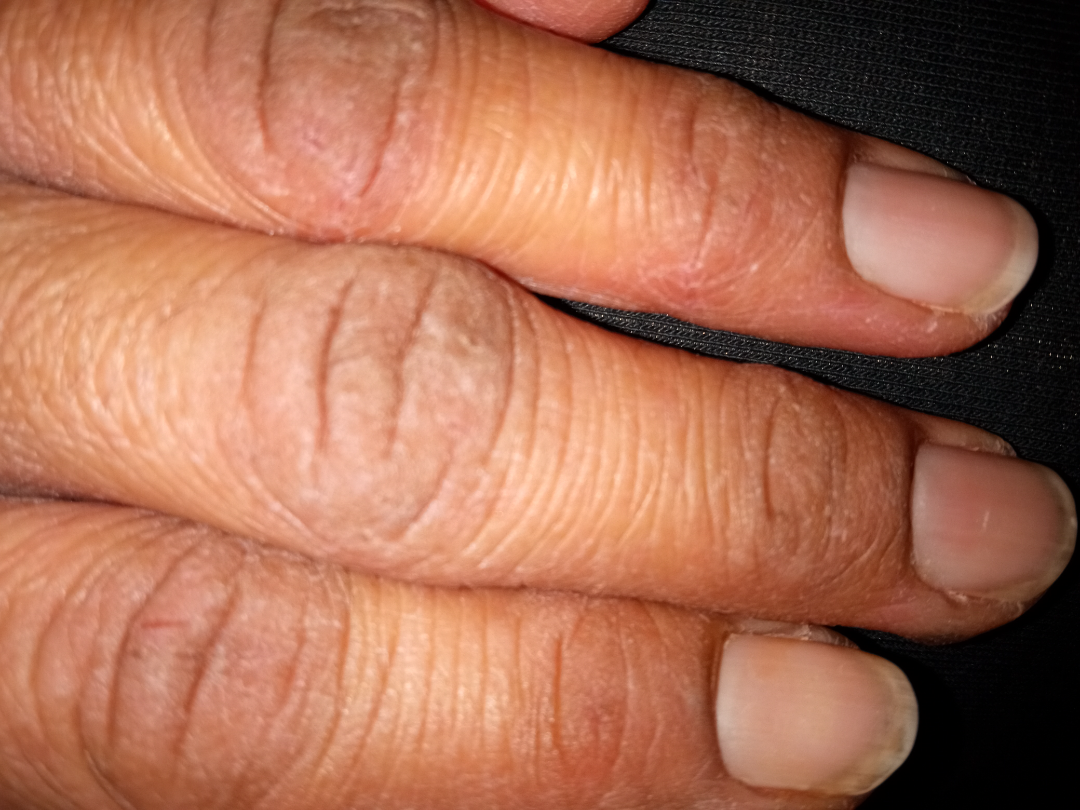Eczema (favored); Irritant Contact Dermatitis (possible); Xerosis (less likely).